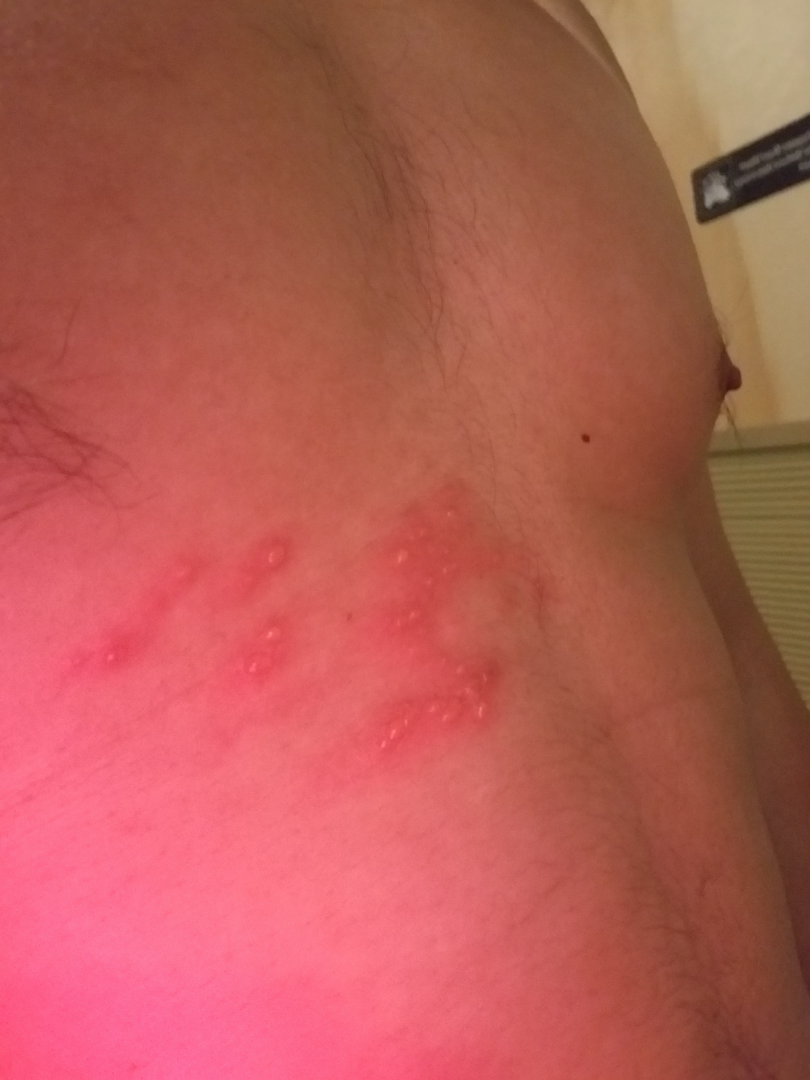{
  "differential": "Herpes Zoster"
}